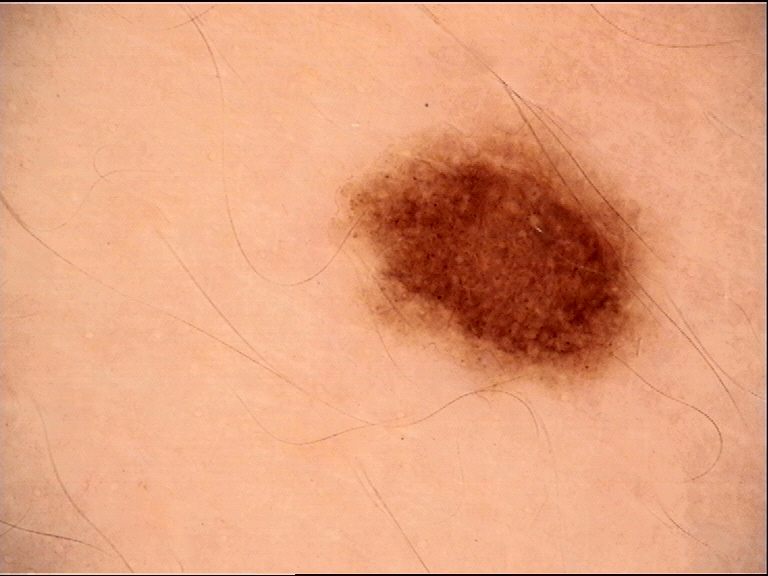- image type — dermatoscopy
- label — dysplastic junctional nevus (expert consensus)